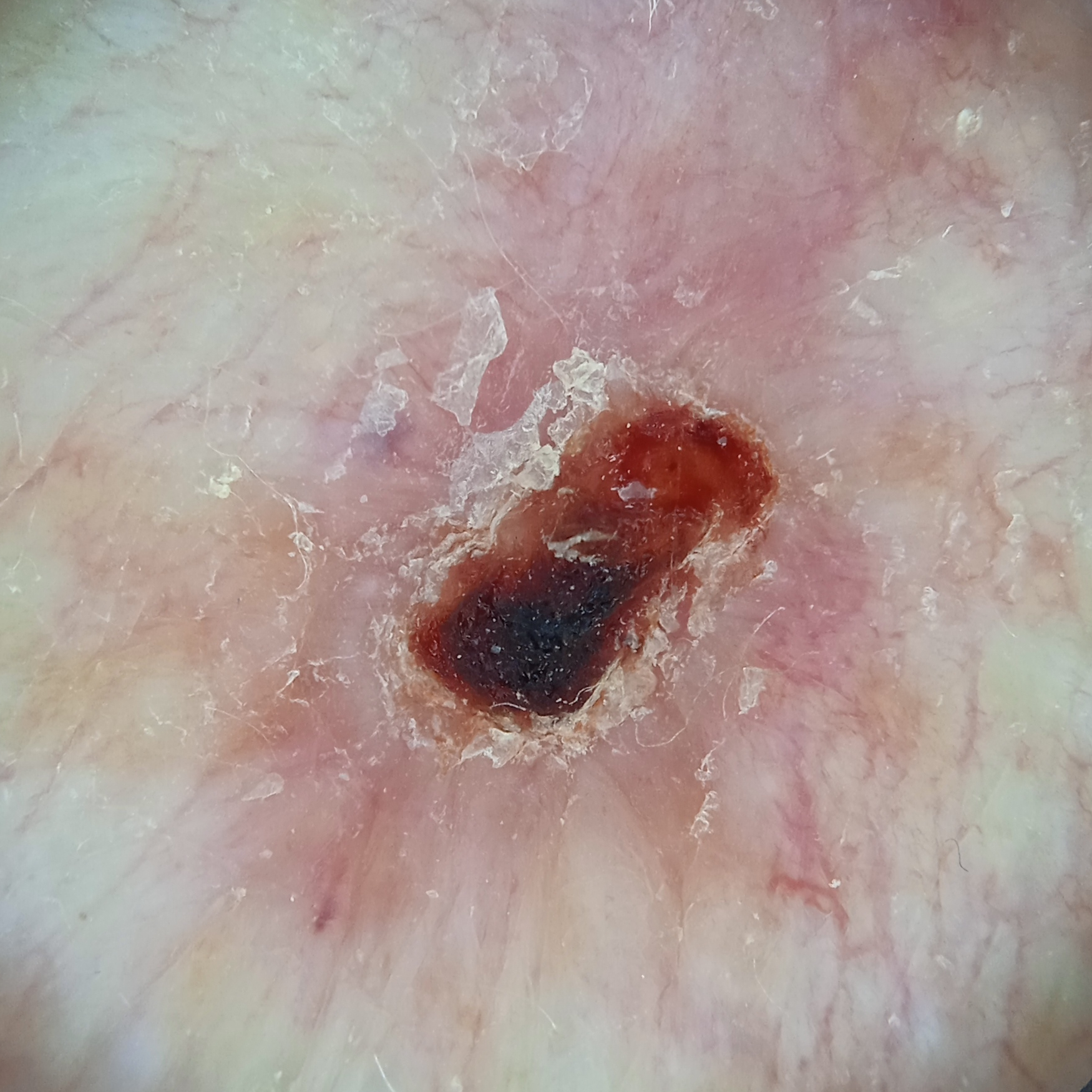patient: male, age 83; imaging: dermatoscopic image; referral: research study (no referral diagnosis); sun reaction: skin reddens with sun exposure; anatomic site: the back; lesion size: 9.5 mm; diagnostic label: basal cell carcinoma (dermatologist consensus).